A dermoscopic photograph of a skin lesion.
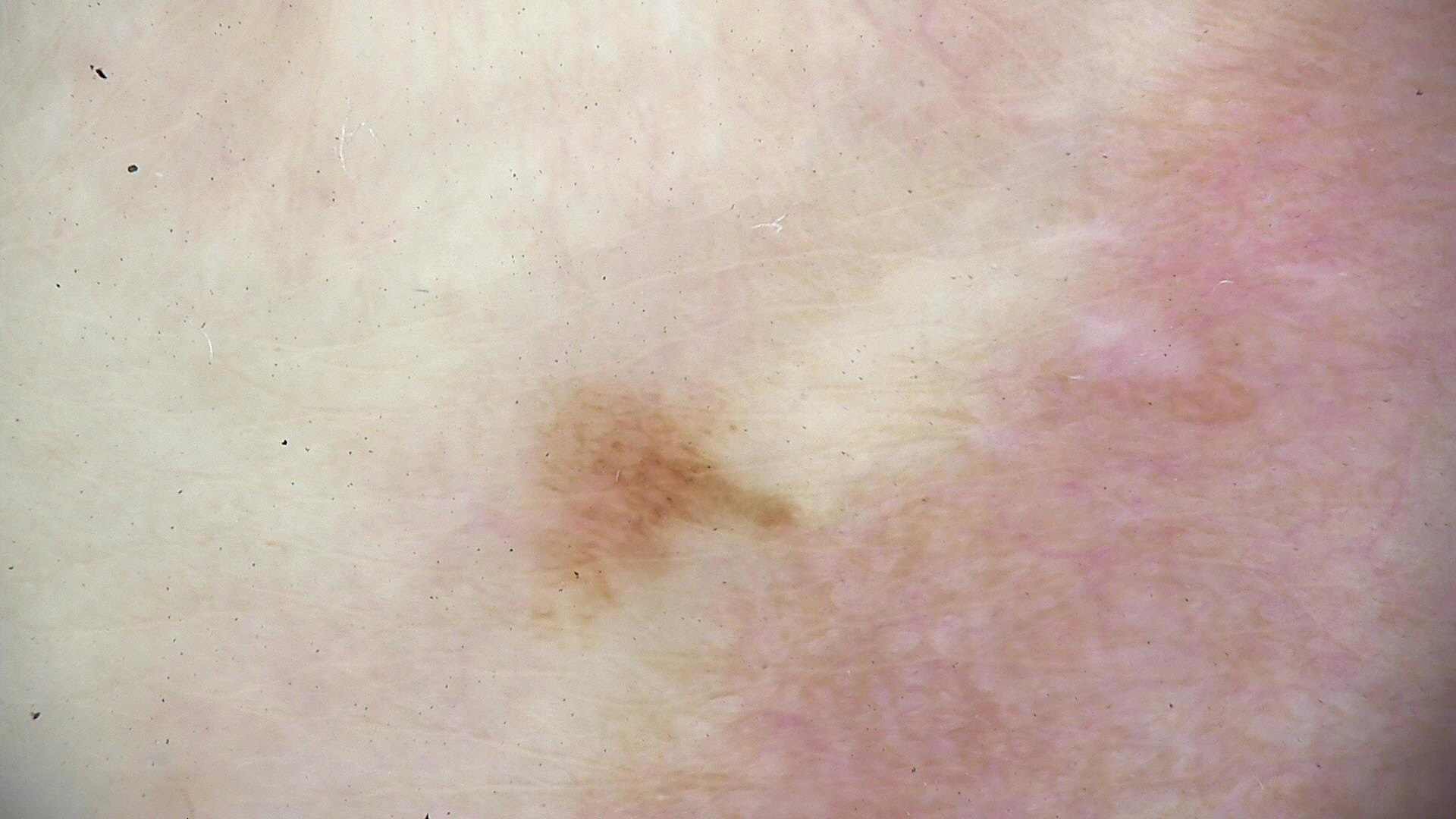Conclusion:
Diagnosed as a benign lesion — an acral dysplastic junctional nevus.